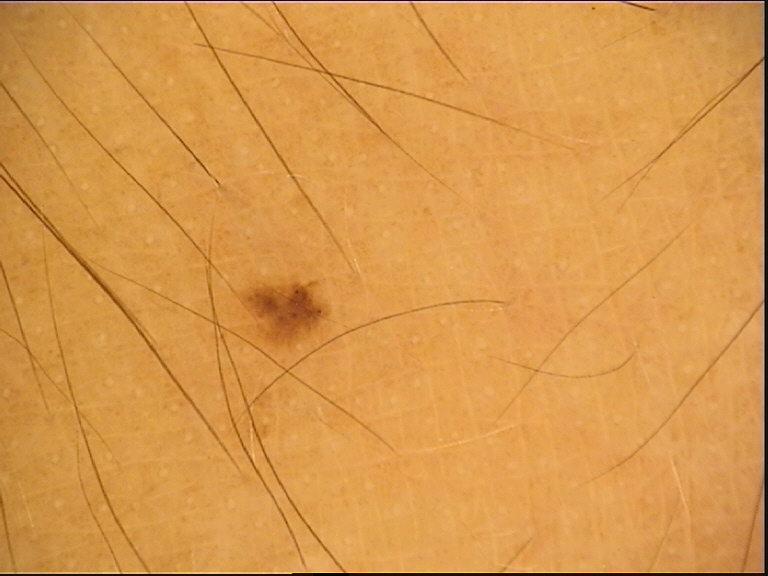Summary:
A dermoscopic photograph of a skin lesion.
Conclusion:
Classified as a dysplastic junctional nevus.